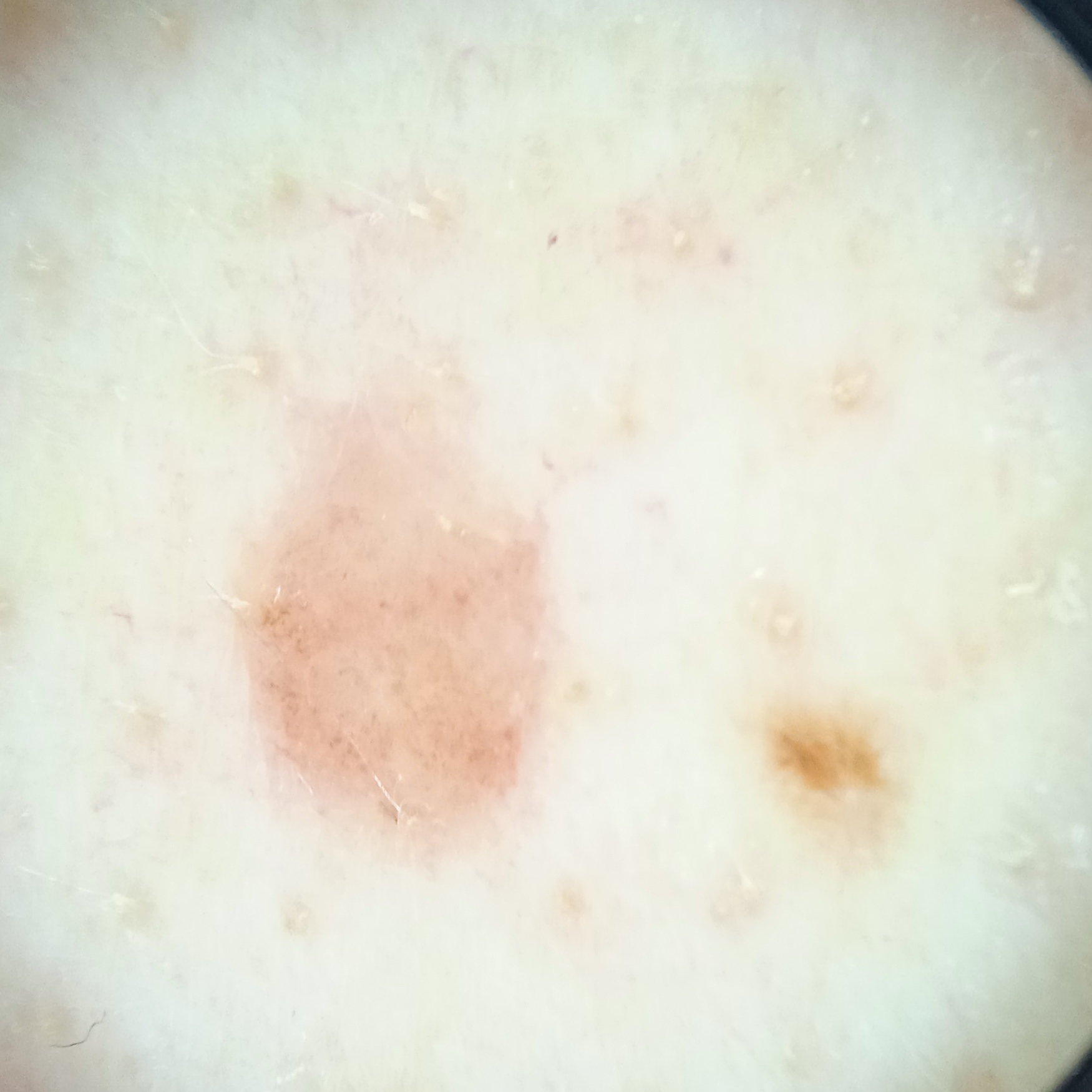Clinical context: A male subject age 65. Collected as part of a research study, without a referral diagnosis. A skin lesion imaged with a dermatoscope. The lesion involves the back. The lesion measures approximately 4.4 mm. Conclusion: Dermatologist review favored a melanocytic nevus.